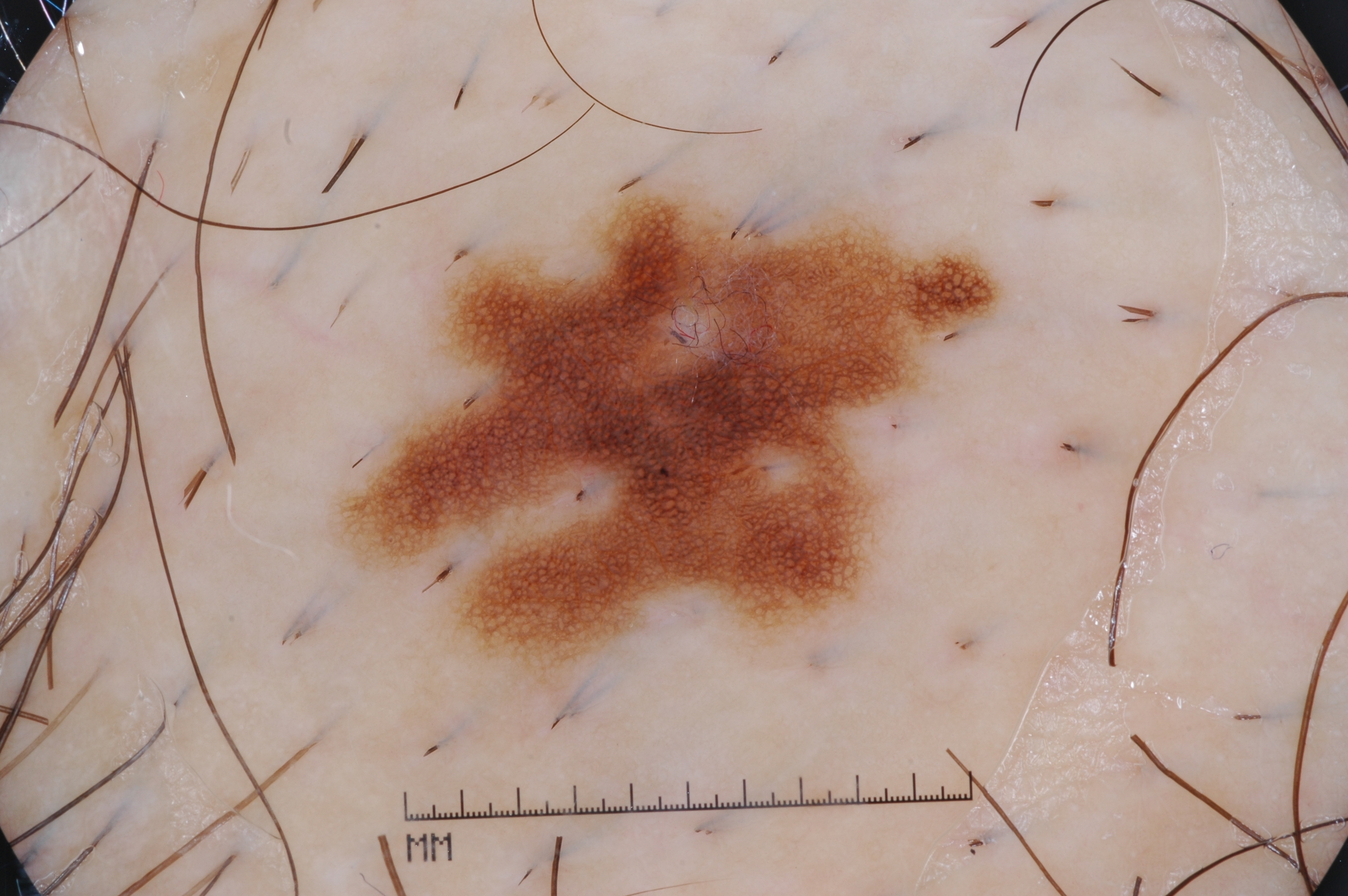Case summary:
The patient is a female approximately 65 years of age. Dermoscopy of a skin lesion. Dermoscopic examination shows pigment network, with no milia-like cysts, streaks, or negative network. The lesion is located at [348, 189, 990, 665].
Impression:
The diagnostic assessment was a melanocytic nevus, a benign lesion.